A female patient roughly 20 years of age. A dermatoscopic image of a skin lesion:
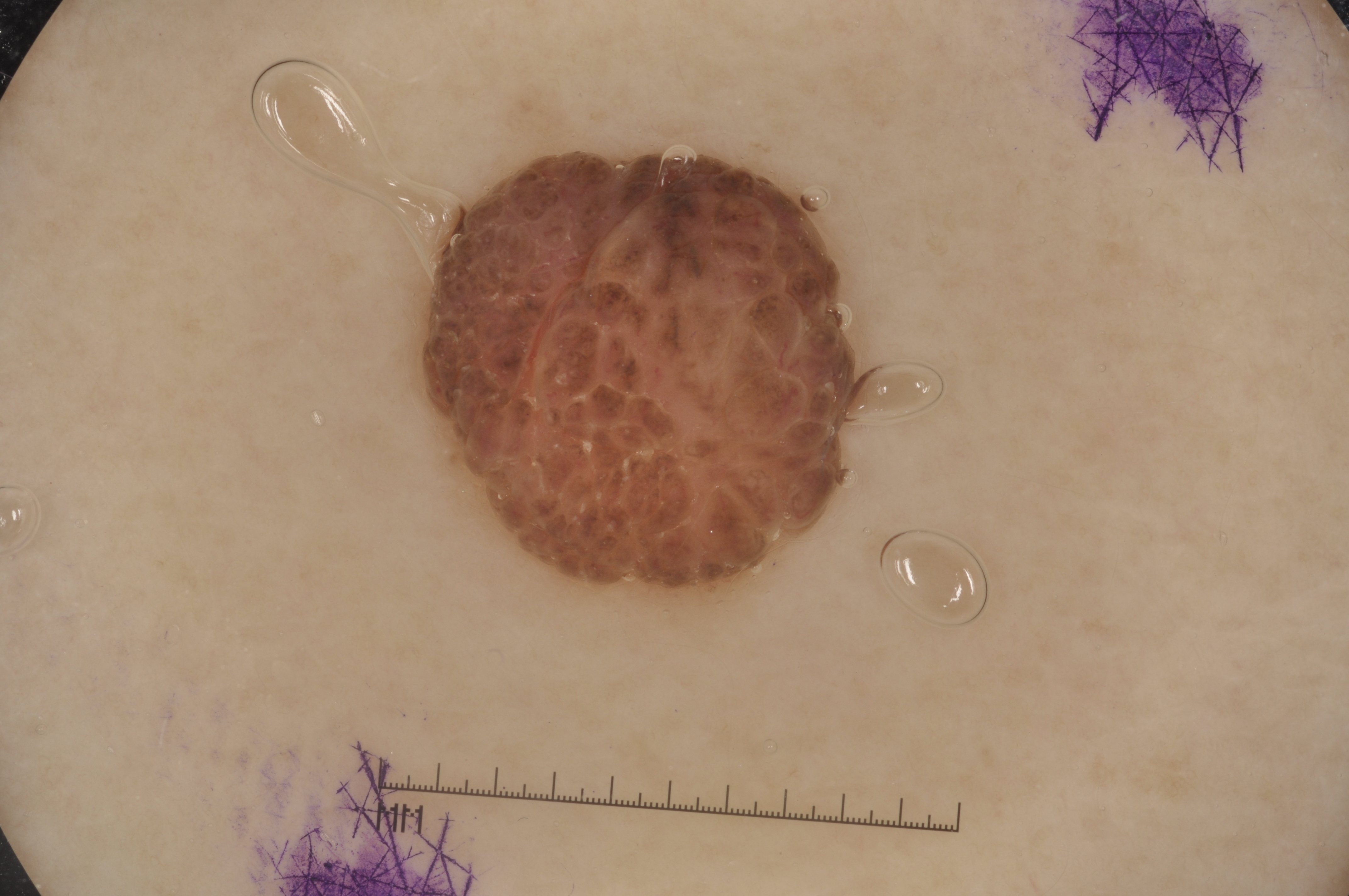Case summary:
- bounding box — x1=411 y1=154 x2=875 y2=602
- dermoscopic features not present — negative network, streaks, milia-like cysts, and pigment network
- impression — a melanocytic nevus, a benign skin lesion